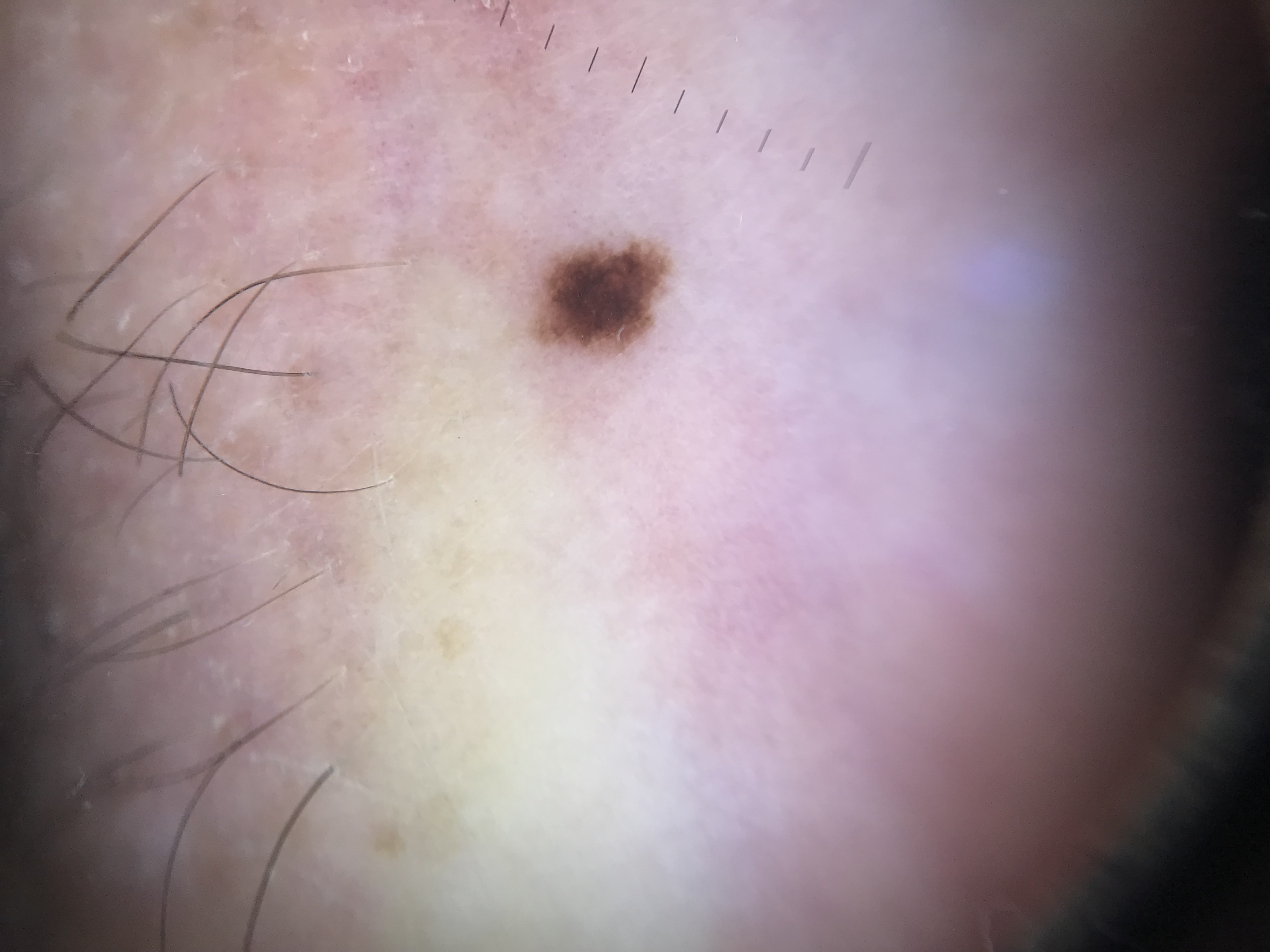diagnosis — junctional nevus (expert consensus).